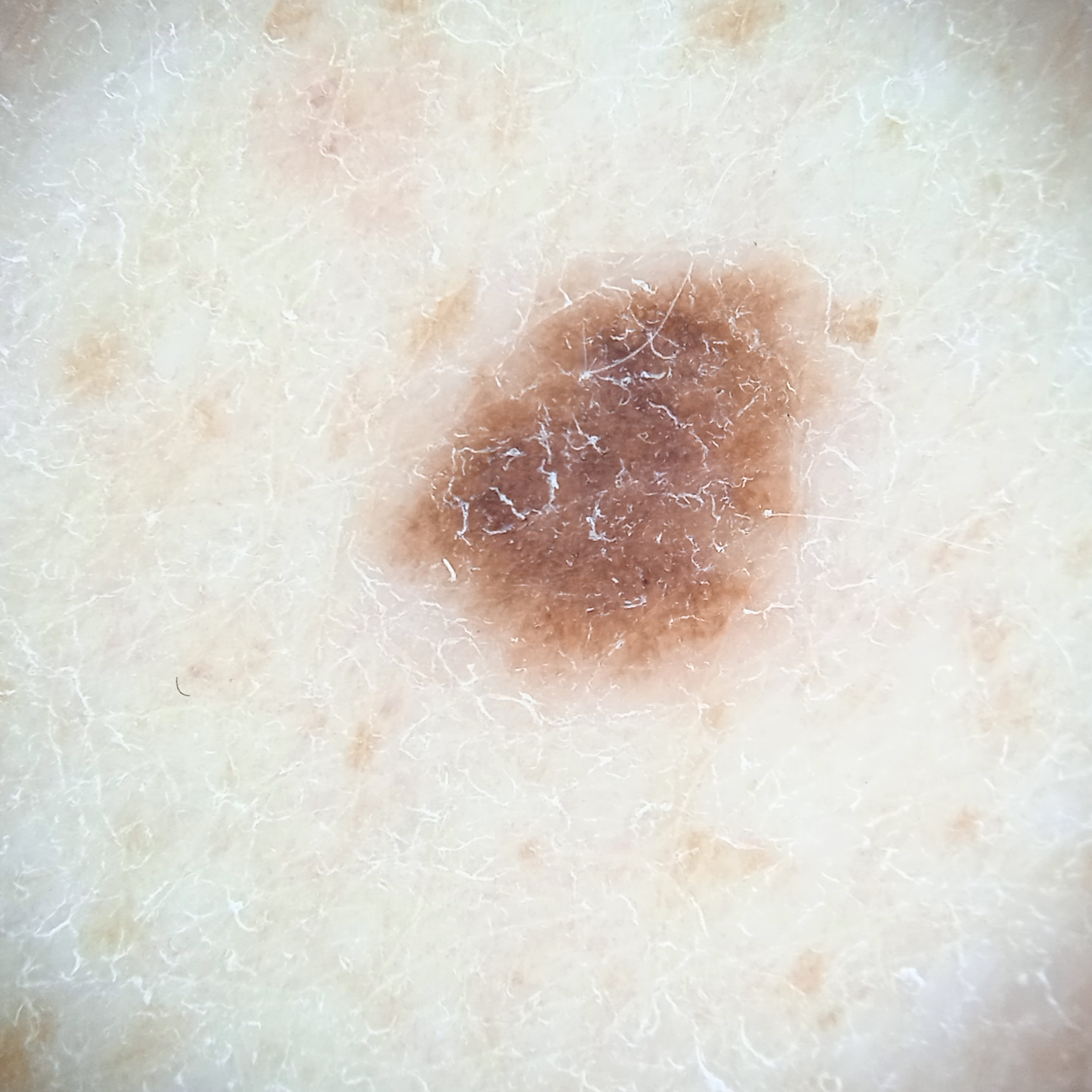| field | value |
|---|---|
| image type | dermoscopy |
| nevus count | few melanocytic nevi overall |
| risk factors | a personal history of cancer, no personal history of skin cancer |
| subject | male, 72 years of age |
| clinical context | research study (no referral diagnosis) |
| lesion size | 5.6 mm |
| assessment | melanocytic nevus (dermatologist consensus) |